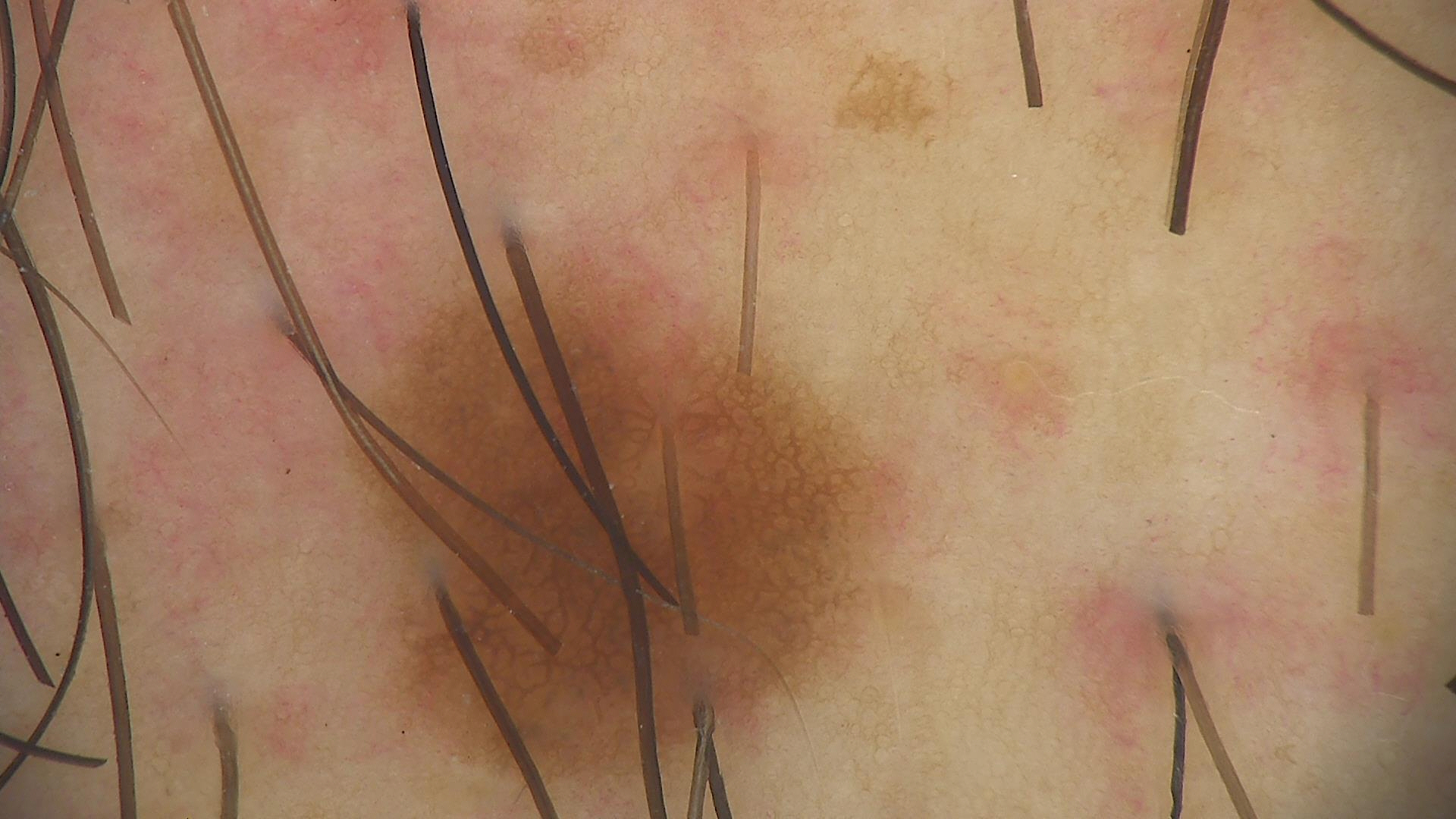Diagnosed as a junctional nevus.